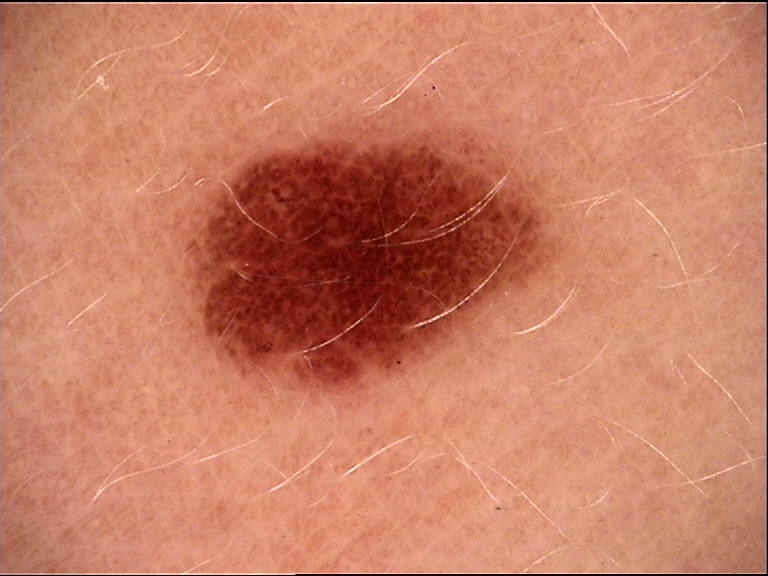Consistent with a junctional nevus.